The patient considered this a rash; texture is reported as raised or bumpy; skin tone: non-clinician graders estimated Monk skin tone scale 4 or 5 (two reviewer pools); the leg is involved; the patient reported no systemic symptoms; the photograph was taken at an angle:
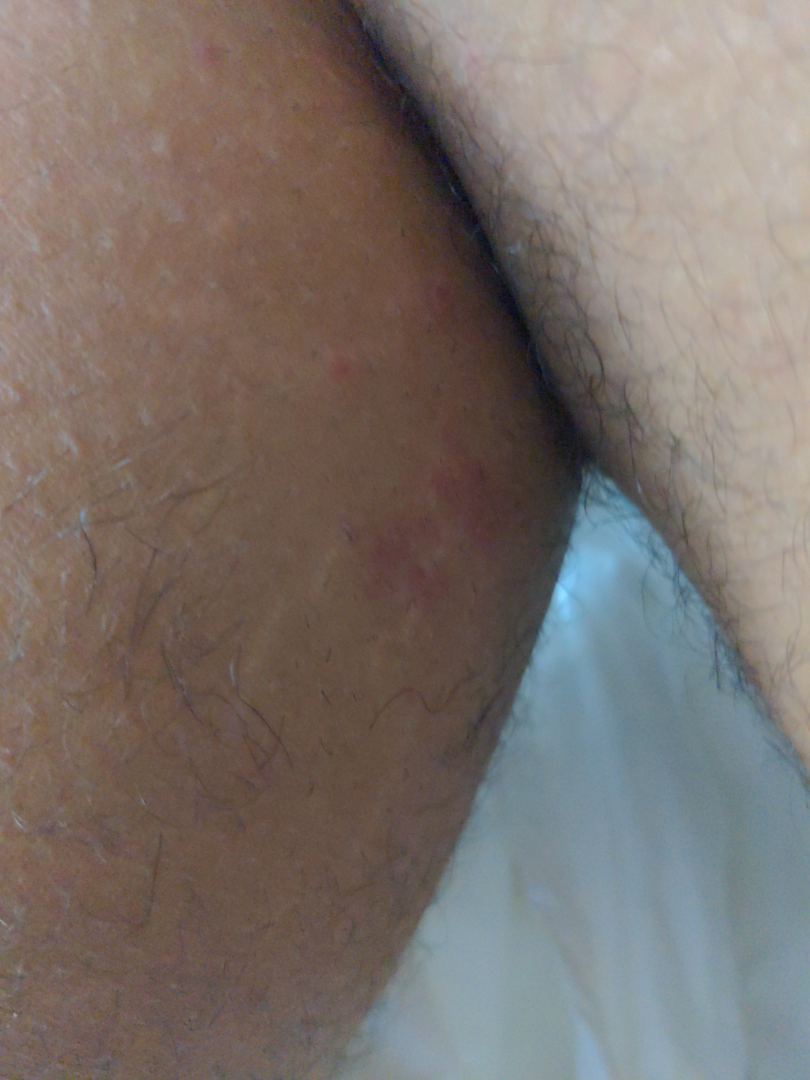The reviewer was unable to grade this case for skin condition.